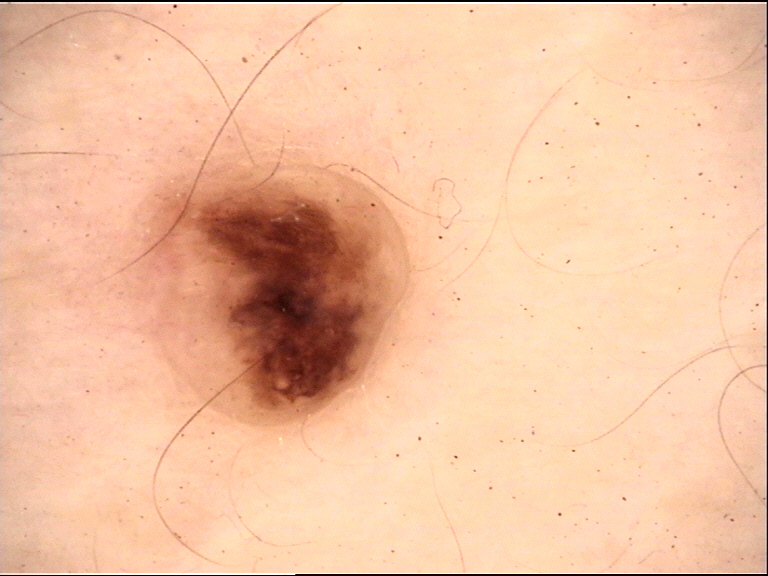A dermoscopic photograph of a skin lesion. Classified as a banal lesion — a dermal nevus.